The photo was captured at a distance · the patient indicates associated fatigue · located on the leg, top or side of the foot, arm and back of the hand · female patient, age 30–39 · the condition has been present for one to three months · texture is reported as rough or flaky and flat · skin tone: non-clinician graders estimated MST 2 or 4.
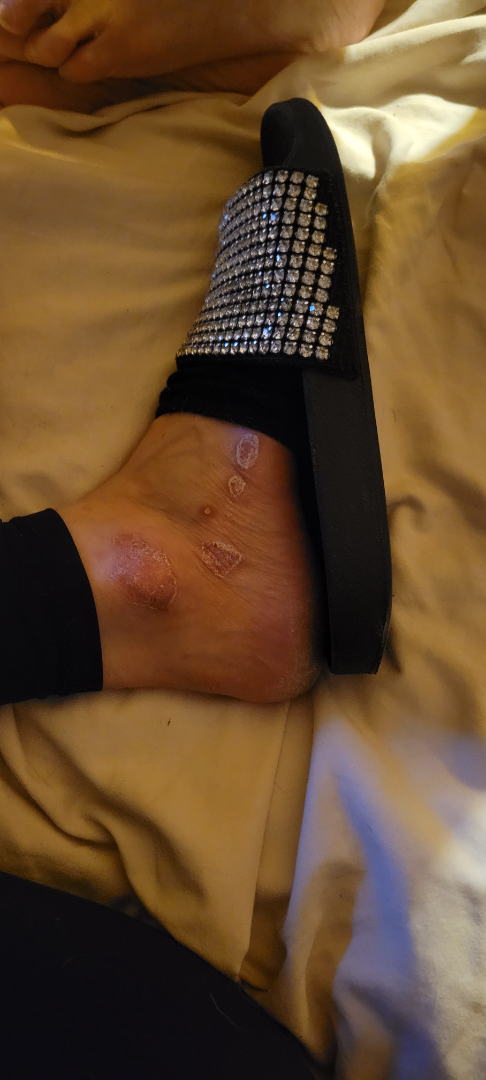Psoriasis (0.54); Tinea (0.23); Eczema (0.23).